This is a close-up image. Fitzpatrick IV: 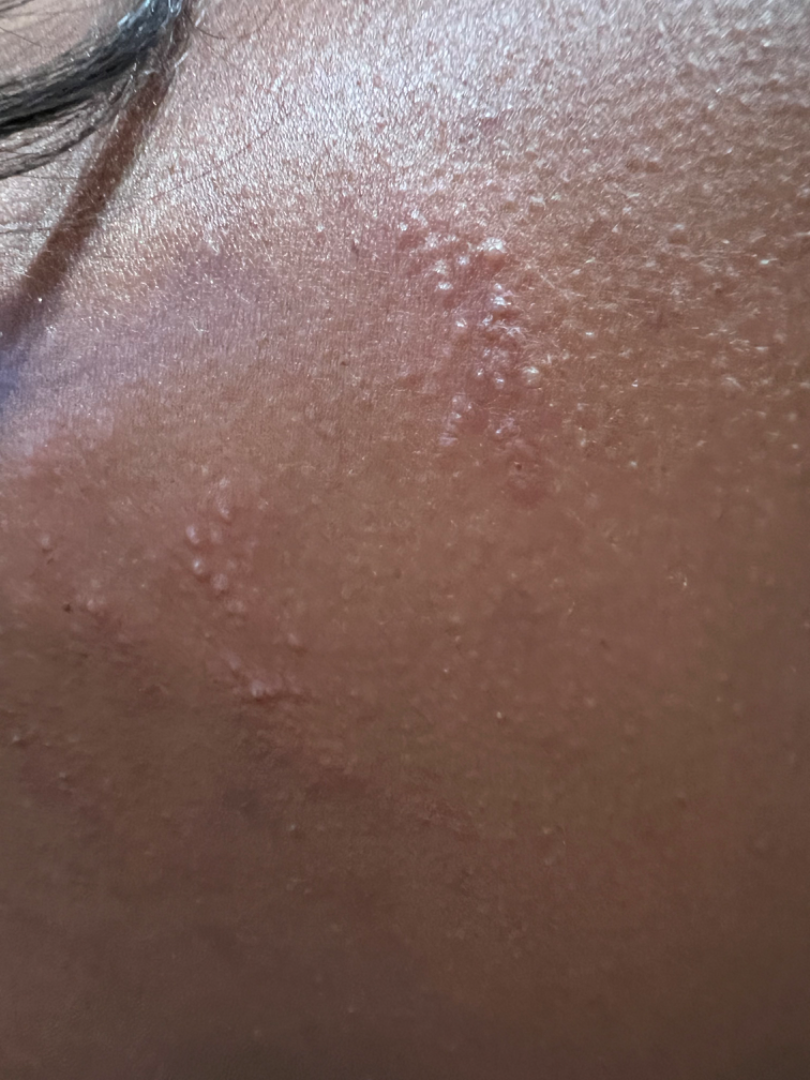Review:
The skin findings could not be characterized from the image.